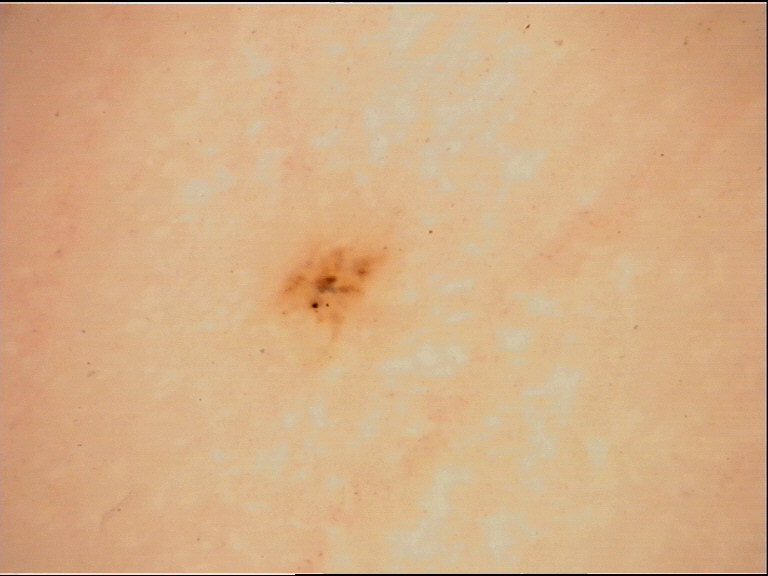A skin lesion imaged with a dermatoscope. Diagnosed as an acral junctional nevus.